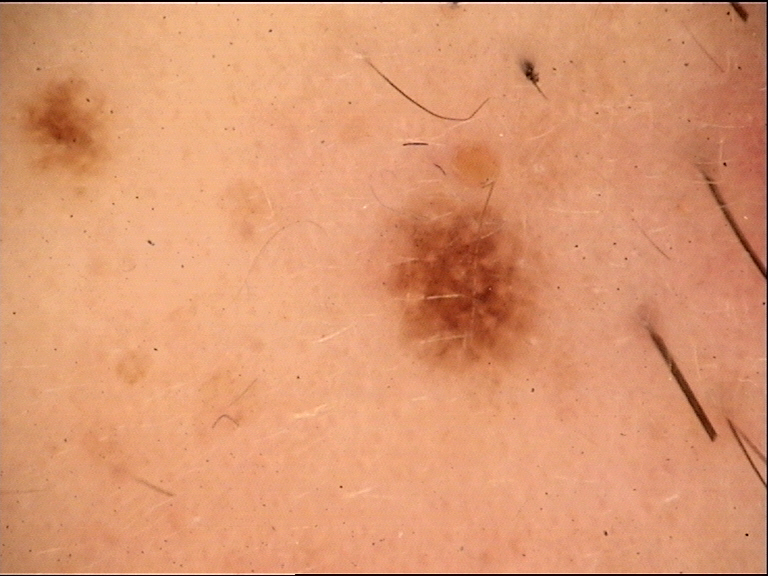The architecture is that of a compound, banal lesion. Labeled as a Miescher nevus.